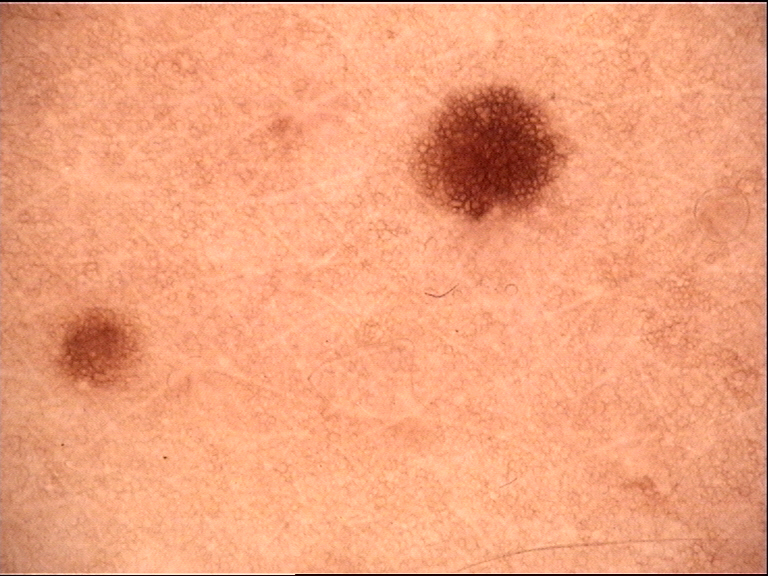A dermoscopic image of a skin lesion.
The morphology is that of a banal lesion.
Diagnosed as a junctional nevus.